Dermoscopy of a skin lesion.
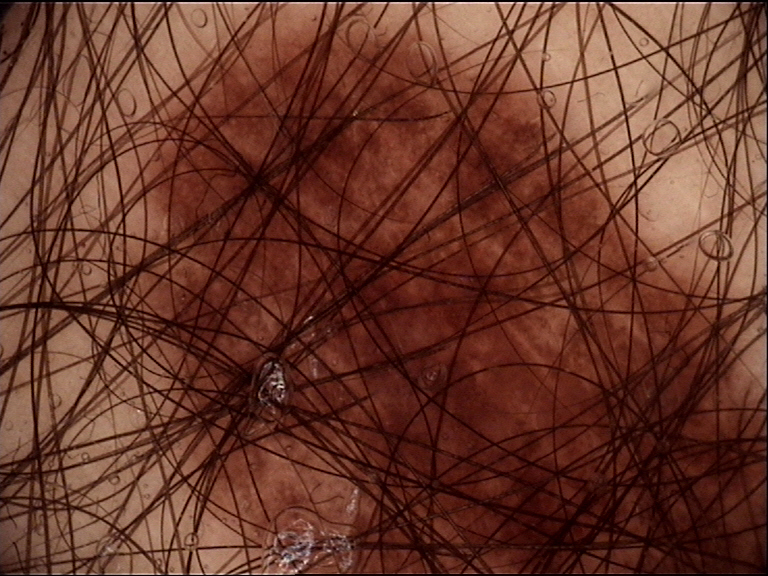Conclusion:
Labeled as a dysplastic junctional nevus.